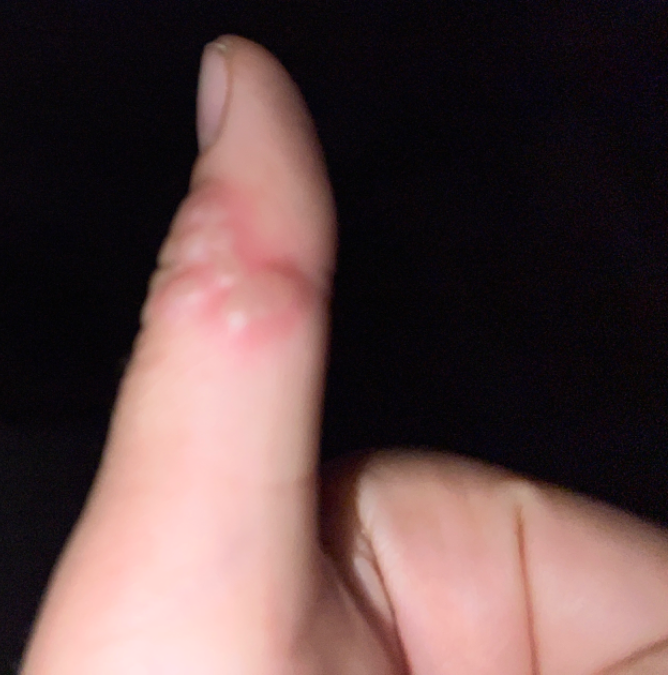differential diagnosis: consistent with Herpes Simplex